Located on the arm, the photo was captured at a distance.
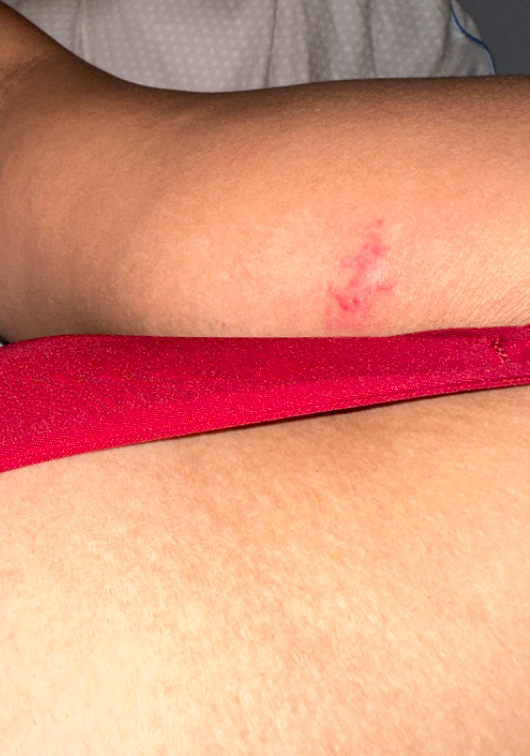Review: On remote review of the image: Insect Bite (0.50); Herpes Simplex (0.50).